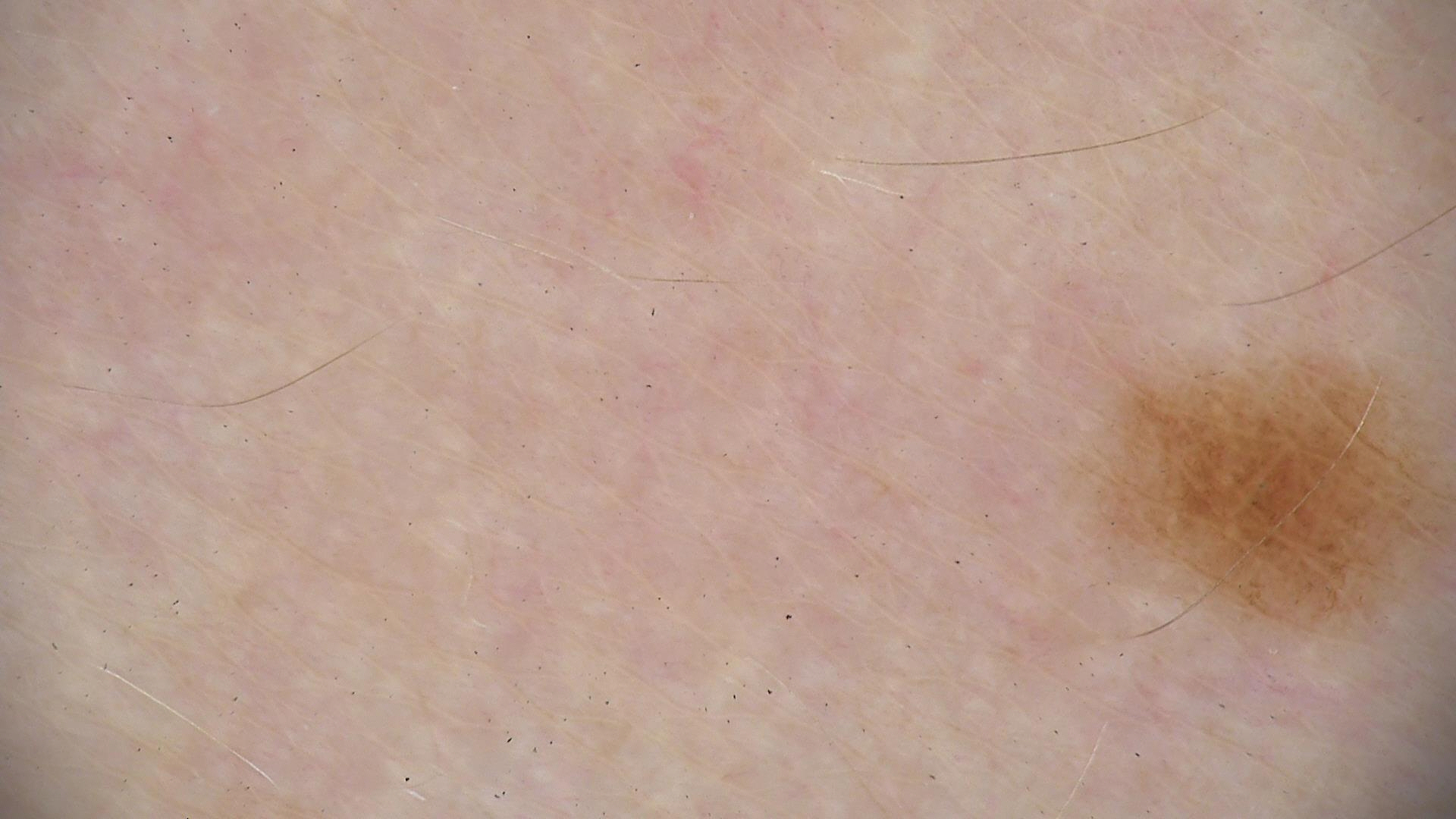<dermoscopy>
  <image>dermoscopy</image>
  <diagnosis>
    <name>dysplastic junctional nevus</name>
    <code>jd</code>
    <malignancy>benign</malignancy>
    <super_class>melanocytic</super_class>
    <confirmation>expert consensus</confirmation>
  </diagnosis>
</dermoscopy>